Reported lesion symptoms include itching, pain, enlargement, bothersome appearance and burning. The contributor reports the condition has been present for one to four weeks. The contributor reports the lesion is rough or flaky. The patient described the issue as a pigmentary problem. The photograph was taken at an angle. The patient is female — 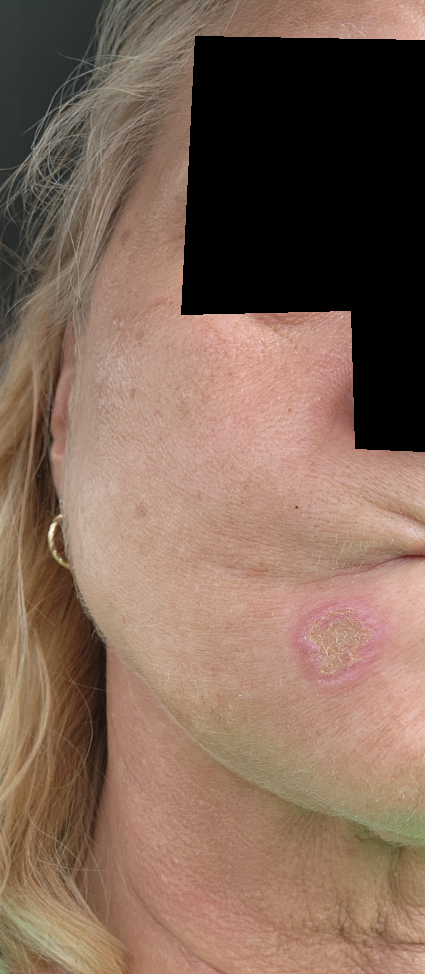On remote review of the image, Eruptive odontogenic cyst (considered); Basal Cell Carcinoma (considered); SCC/SCCIS (considered).